The patient reported no systemic symptoms · reported duration is less than one week · a close-up photograph · the lesion involves the arm · the patient described the issue as a rash · the lesion is associated with bothersome appearance · male contributor, age 18–29: 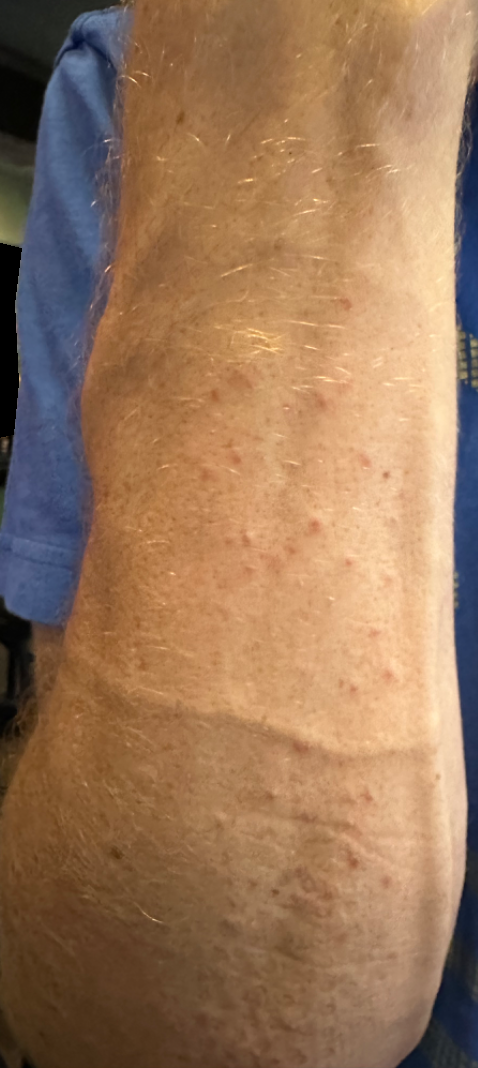On photographic review: Hypersensitivity, Insect Bite and Allergic Contact Dermatitis were considered with similar weight.